The photo was captured at an angle; self-categorized by the patient as a rash; texture is reported as rough or flaky; the condition has been present for one to three months; no relevant lesion symptoms reported; the lesion involves the back of the hand:
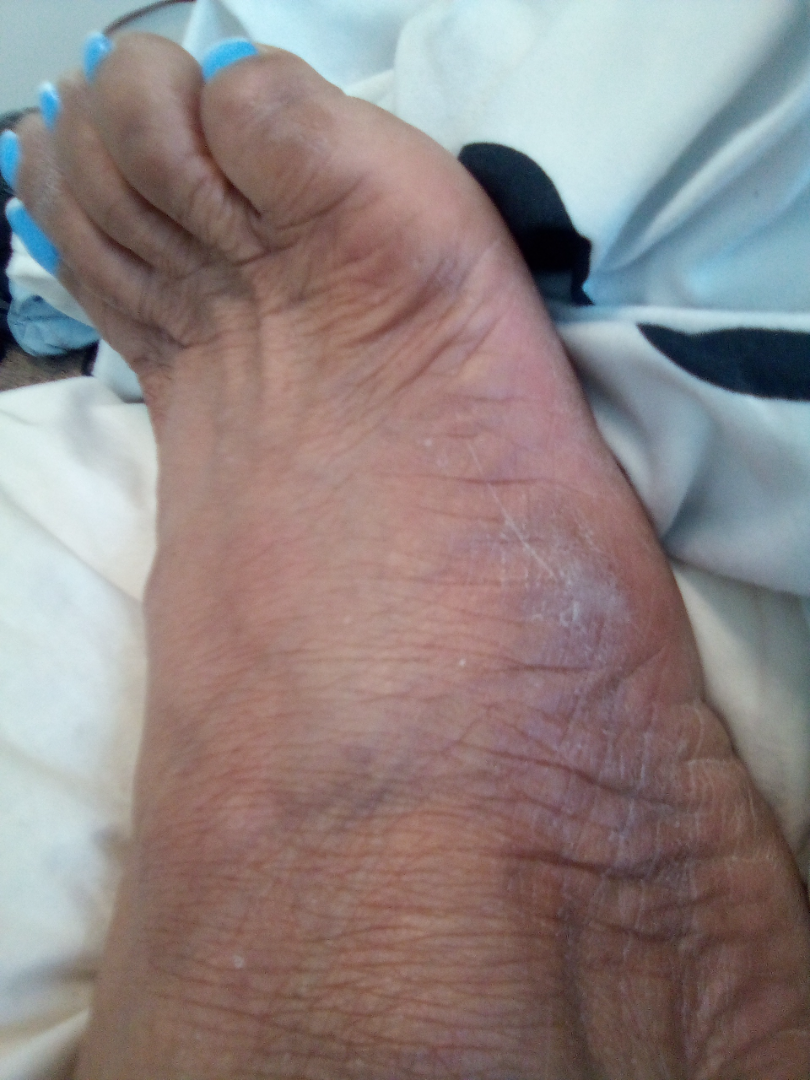differential — the favored diagnosis is Verruca vulgaris; with consideration of Lichen Simplex Chronicus.